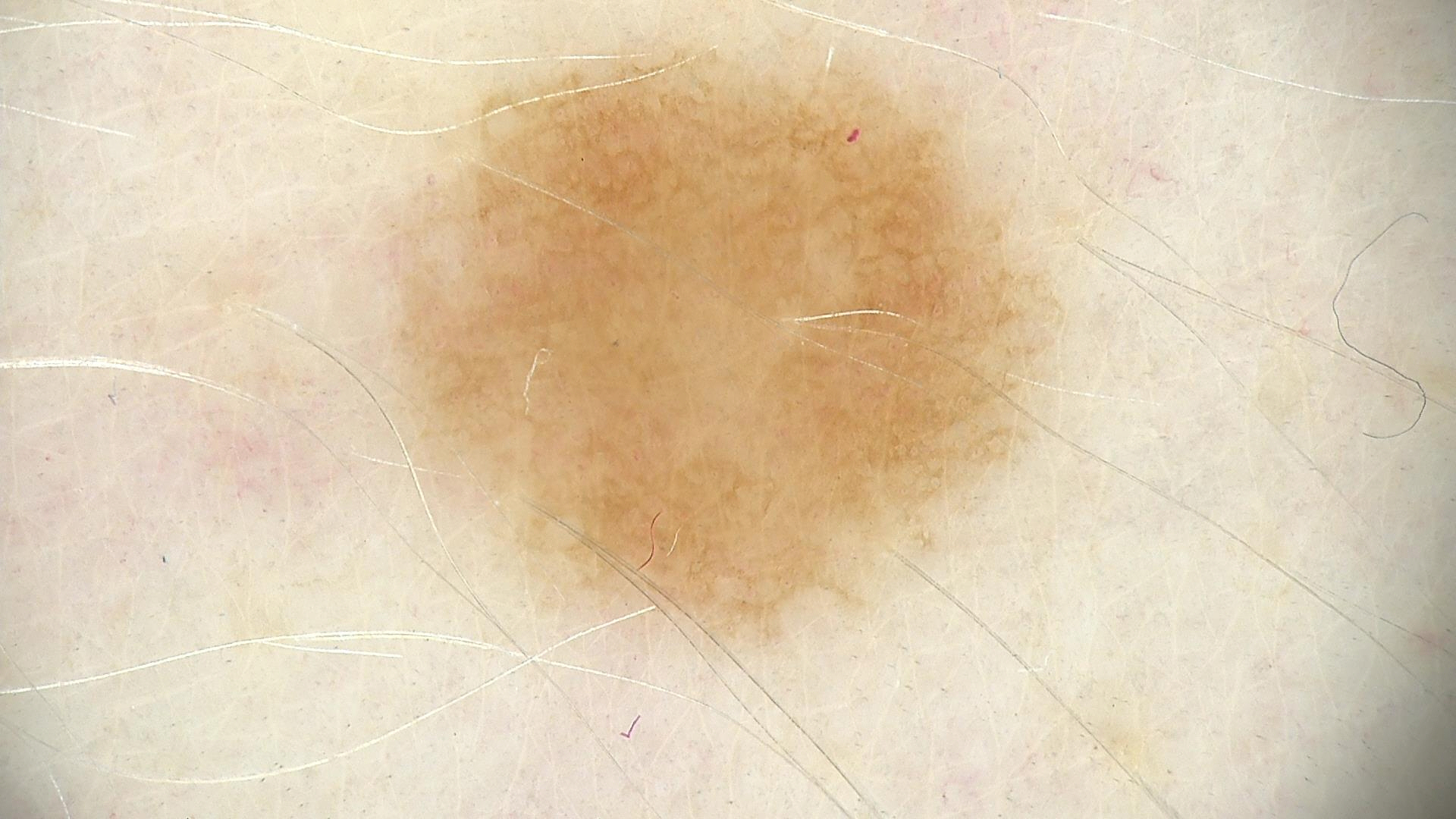image=dermoscopy
diagnosis=junctional nevus (expert consensus)